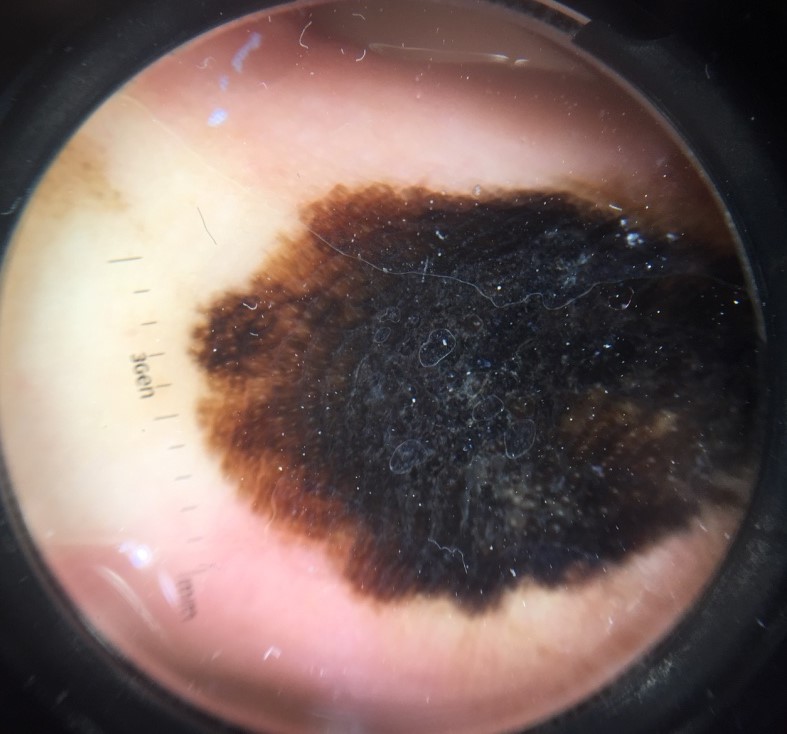pathology = acral lentiginous melanoma (biopsy-proven)